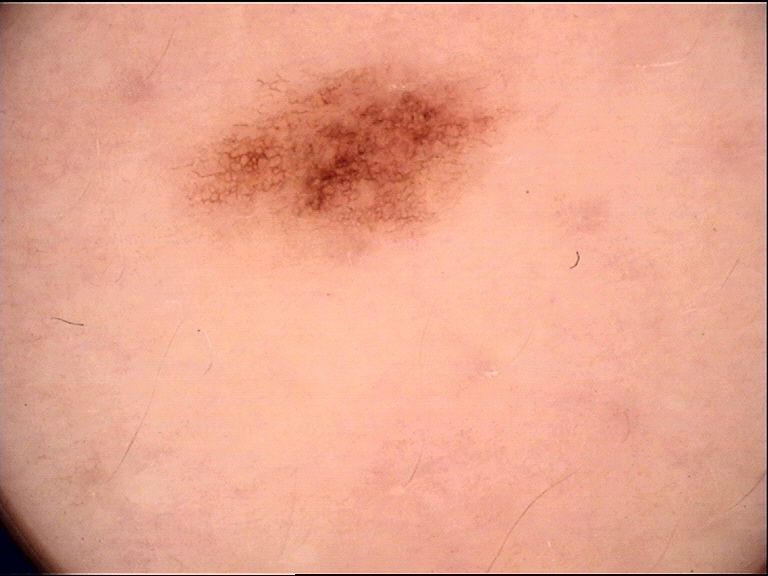image=dermatoscopy | label=dysplastic junctional nevus (expert consensus).